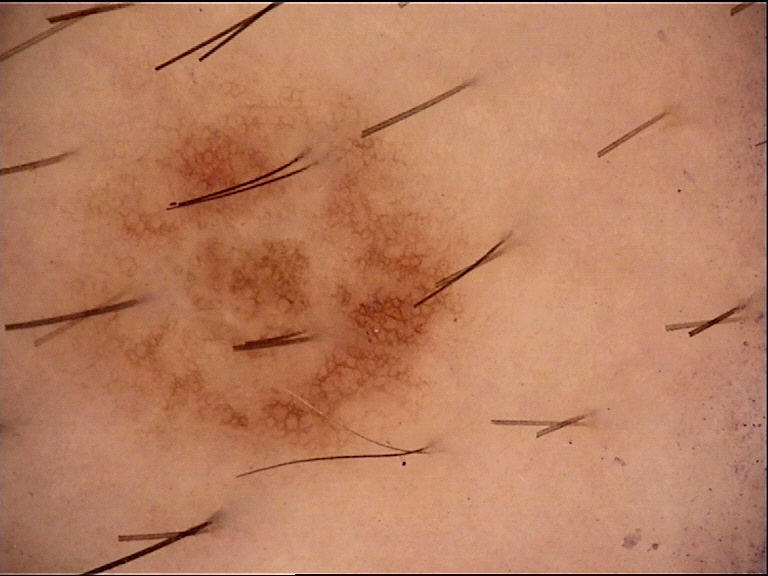The diagnosis was a dysplastic compound nevus.